A clinical overview photograph of a skin lesion · a female patient aged approximately 70.
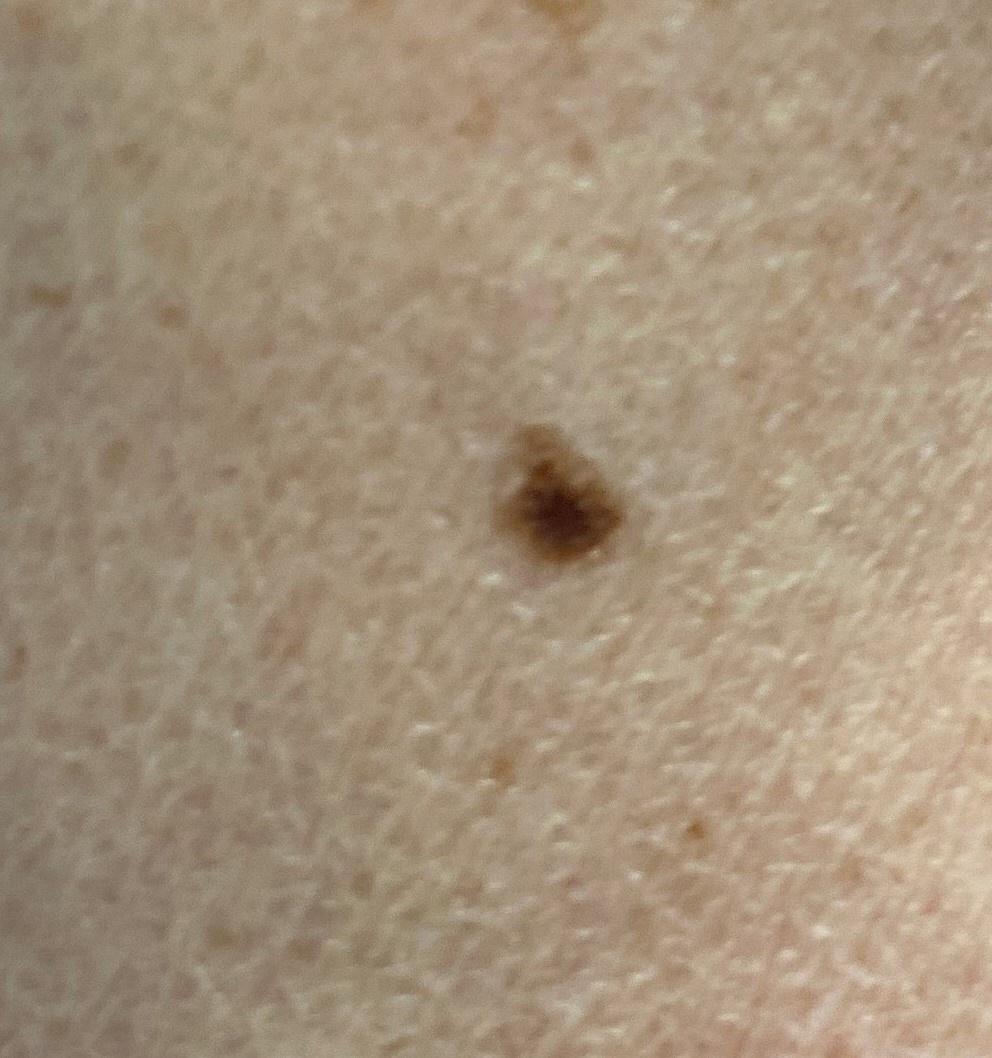Clinical context: The lesion involves an upper extremity. Impression: Consistent with a nevus.